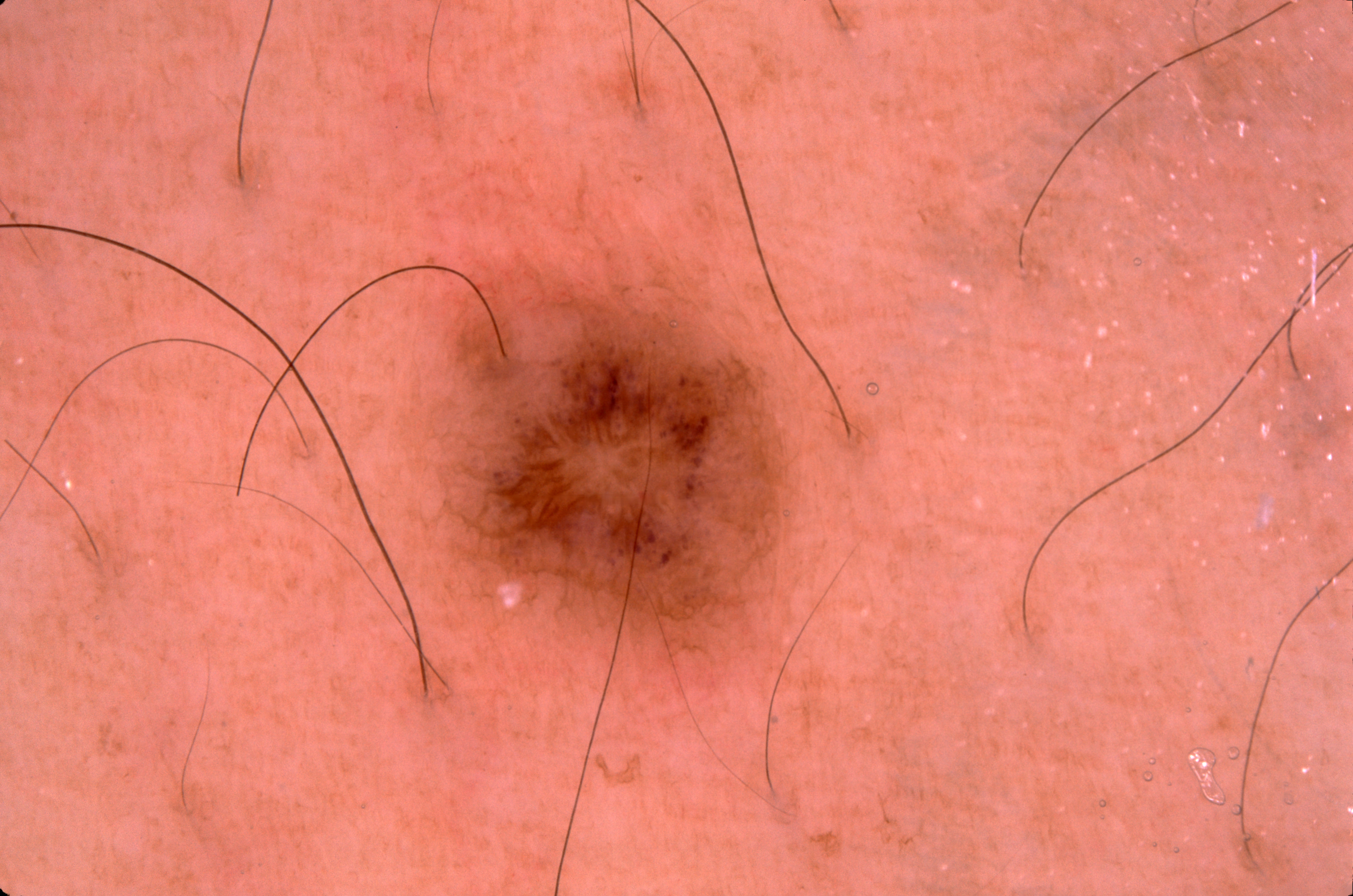A female subject aged approximately 50.
A skin lesion imaged with a dermatoscope.
On dermoscopy, the lesion shows pigment network; no milia-like cysts, streaks, or negative network.
With coordinates (x1, y1, x2, y2), the lesion occupies the region 430, 275, 793, 663.
Consistent with a melanocytic nevus, a benign lesion.